A dermoscopic close-up of a skin lesion.
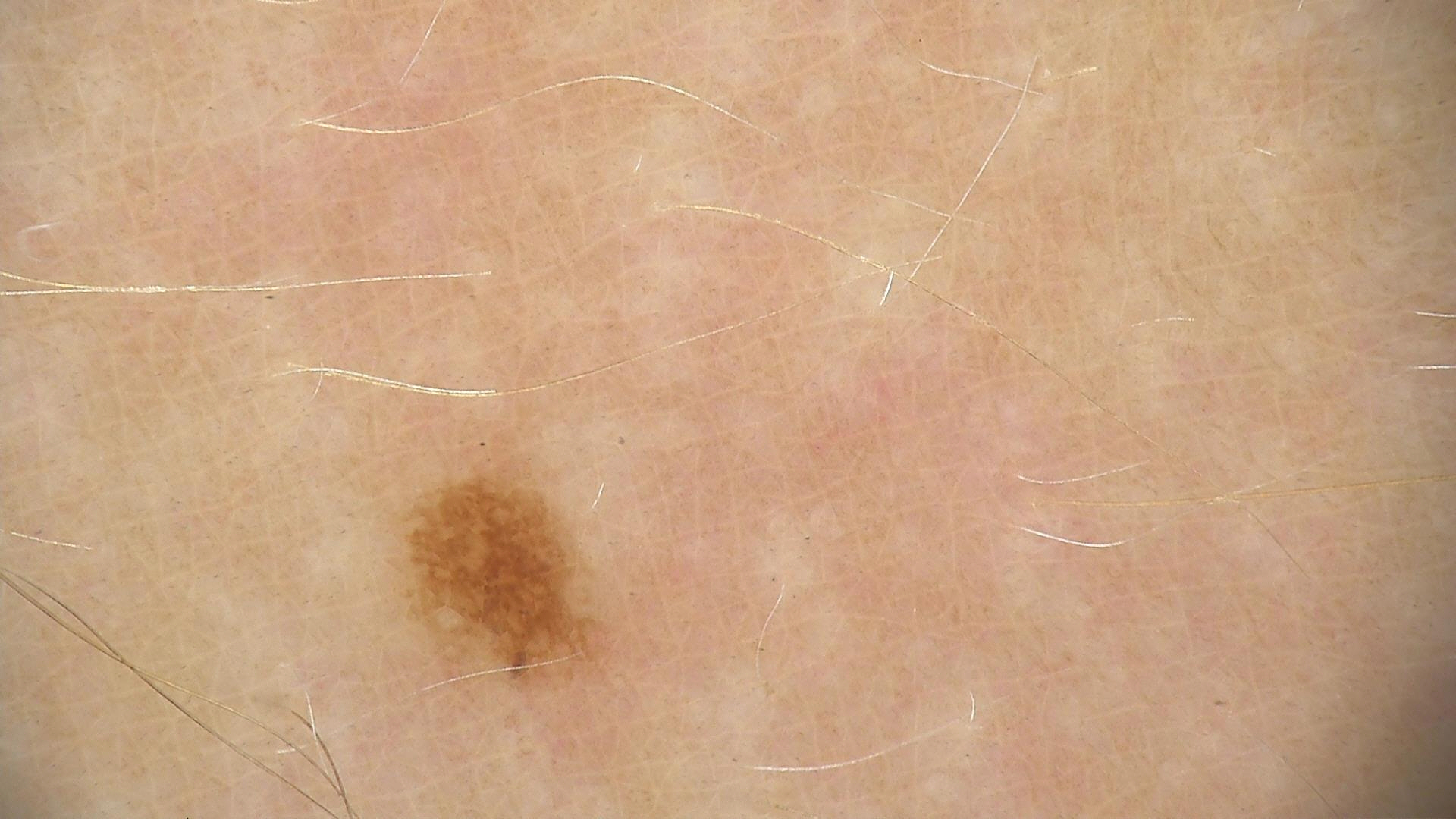| key | value |
|---|---|
| label | dysplastic junctional nevus (expert consensus) |